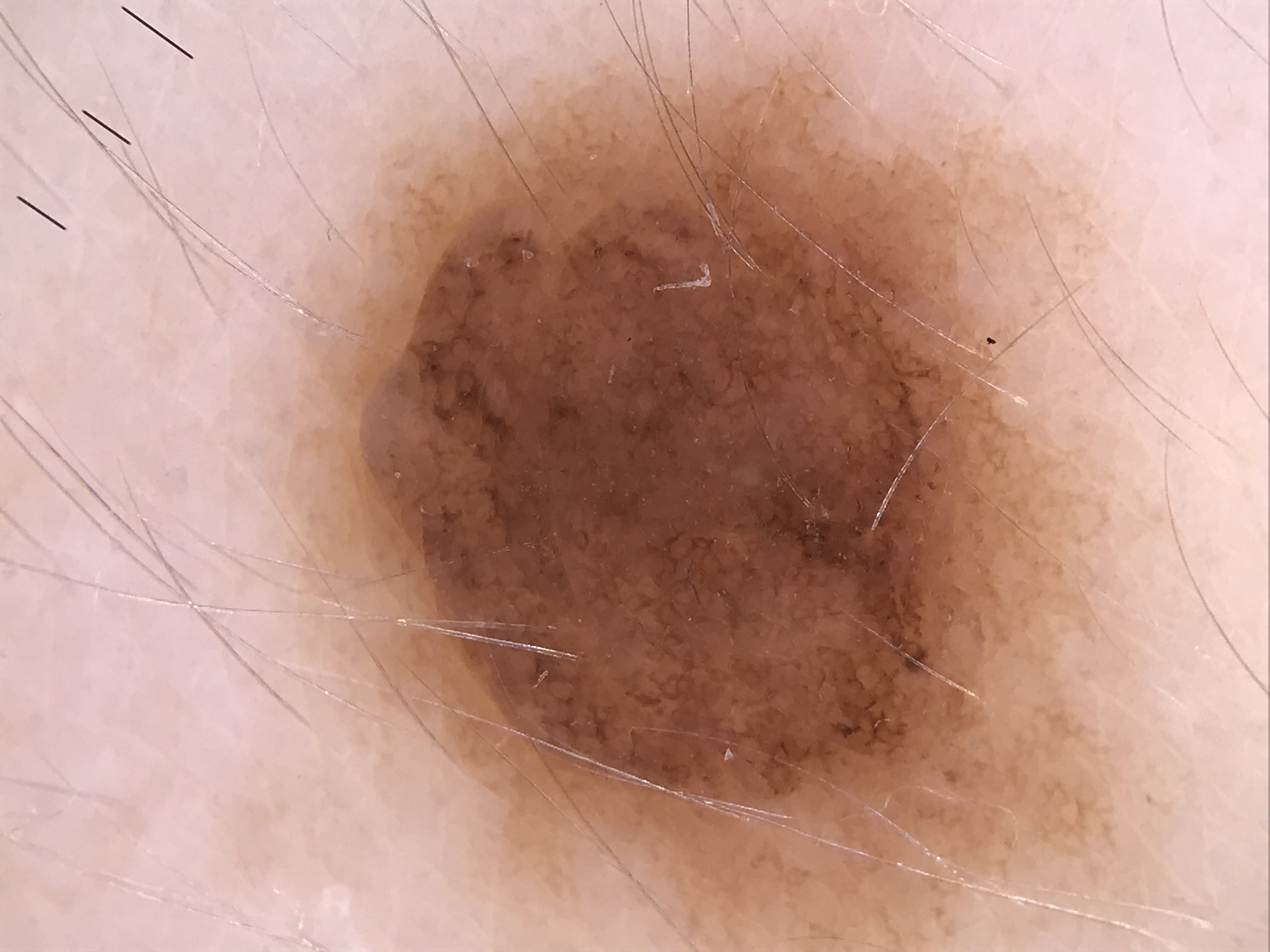Findings:
A dermoscopy image of a single skin lesion.
Conclusion:
The diagnosis was a banal lesion — a compound nevus.